A skin lesion imaged with a dermatoscope.
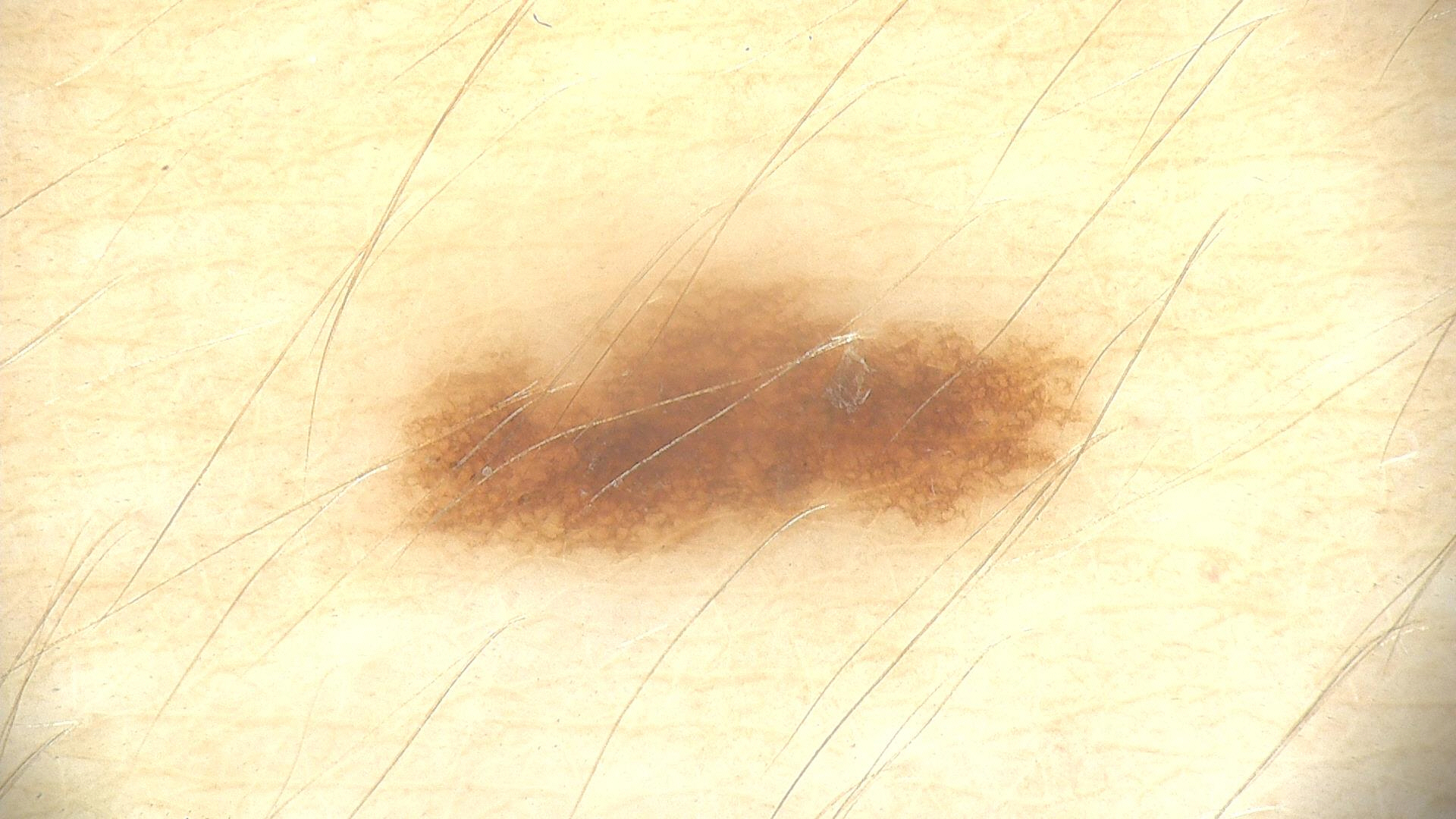Classified as a dysplastic junctional nevus.